The subject is a male aged 40–49, the photograph is a close-up of the affected area, the lesion involves the arm:
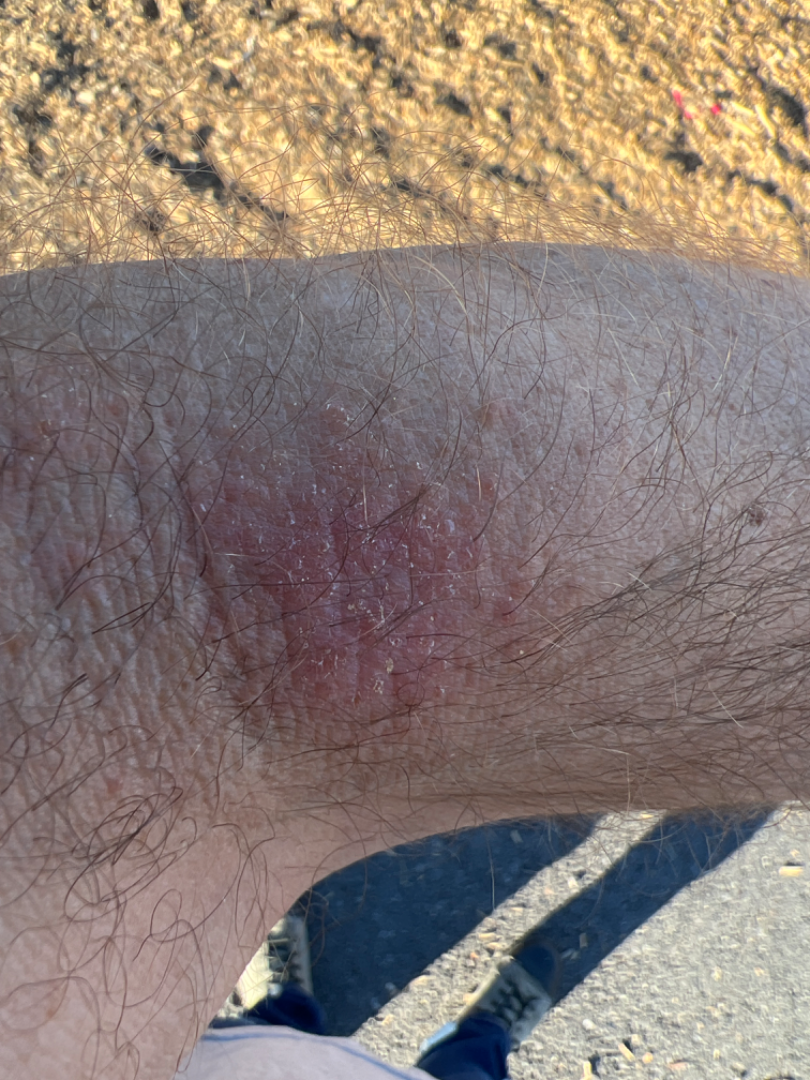Reviewed remotely by one dermatologist: in keeping with Allergic Contact Dermatitis.